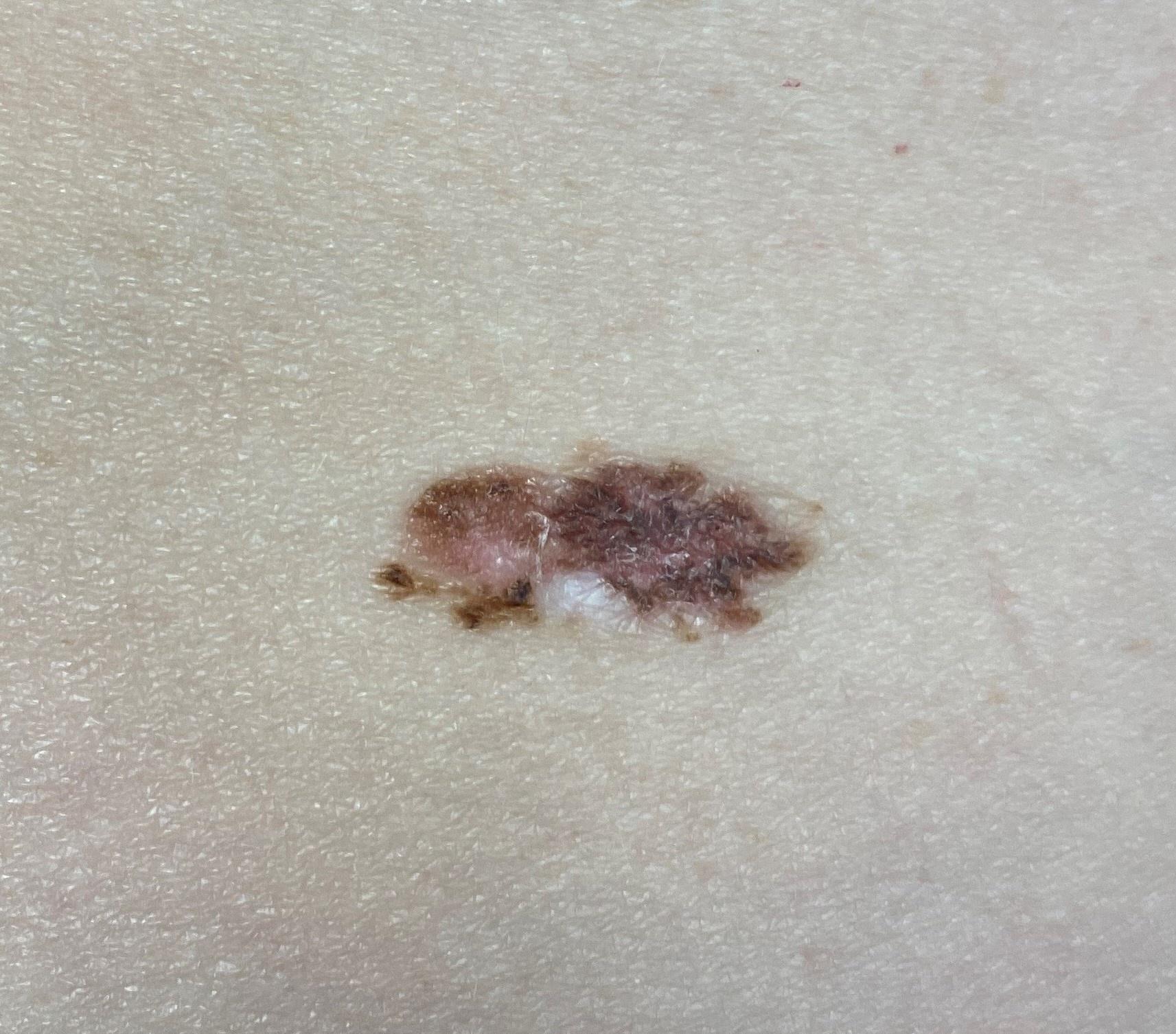image type: clinical photo (overview)
relevant background: a prior melanoma
skin type: II
site: the anterior trunk
diagnosis: Melanoma (biopsy-proven)